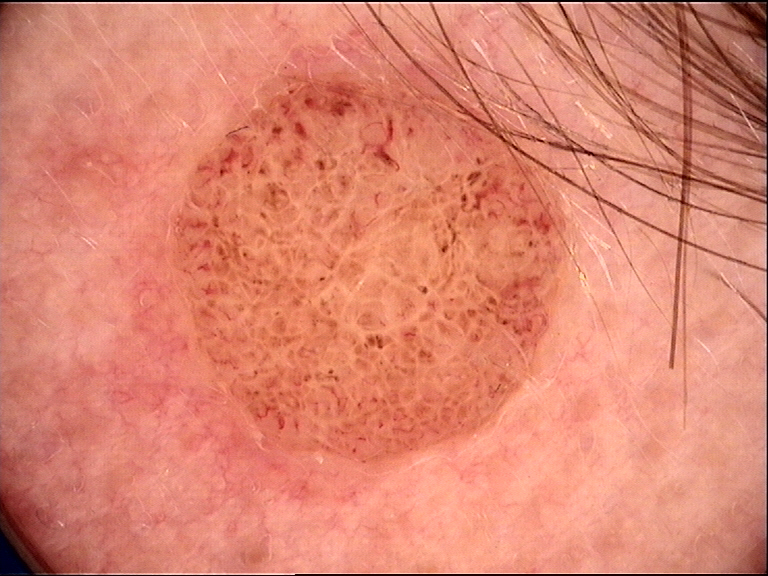A dermoscopy image of a single skin lesion. Consistent with a banal lesion — a dermal nevus.